A female patient about 60 years old; this is a dermoscopic photograph of a skin lesion — 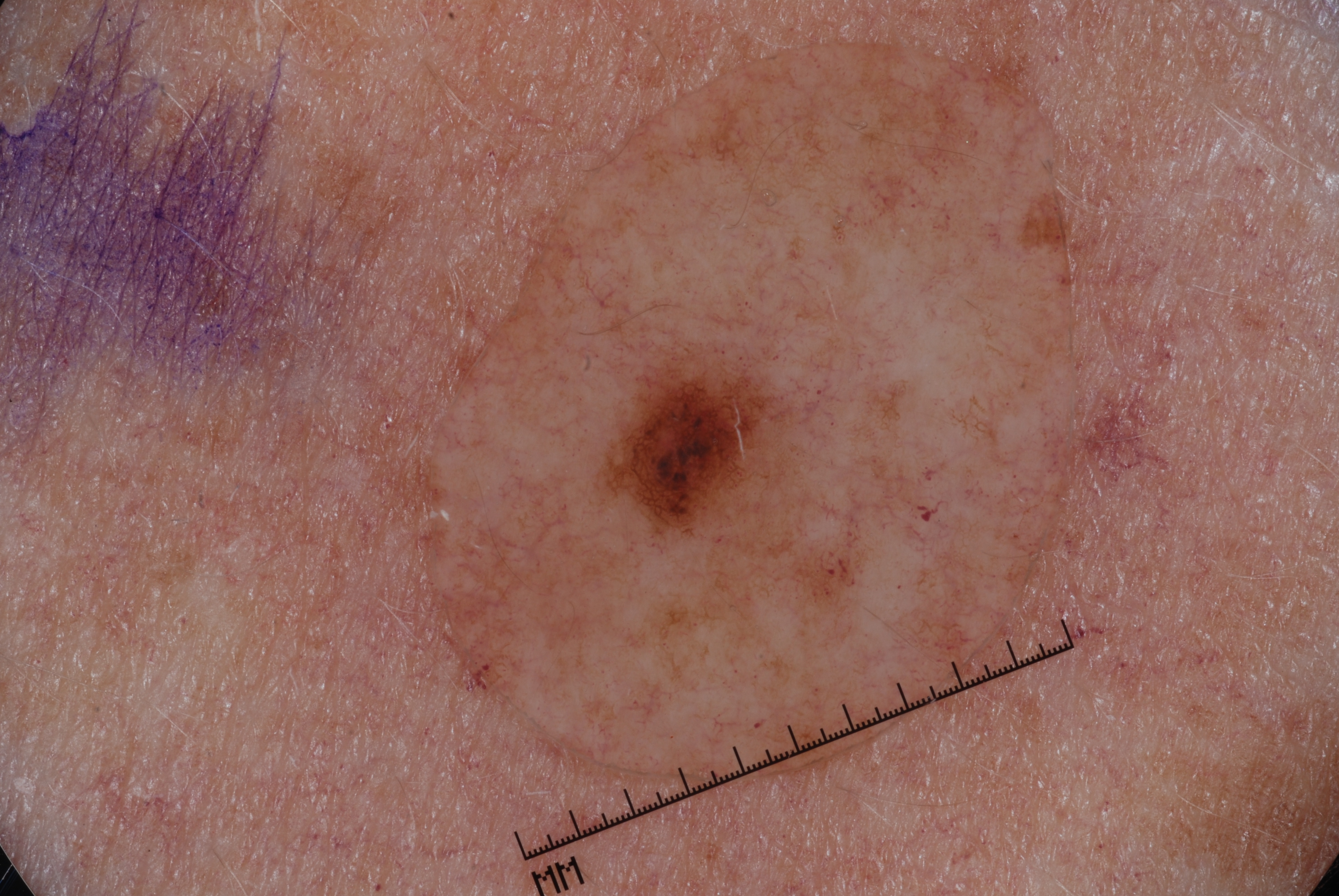A small lesion within a wider field of skin. The lesion is bounded by bbox=[587, 335, 809, 550]. Dermoscopic examination shows pigment network, with no milia-like cysts, negative network, or streaks. Consistent with a melanocytic nevus, a benign lesion.